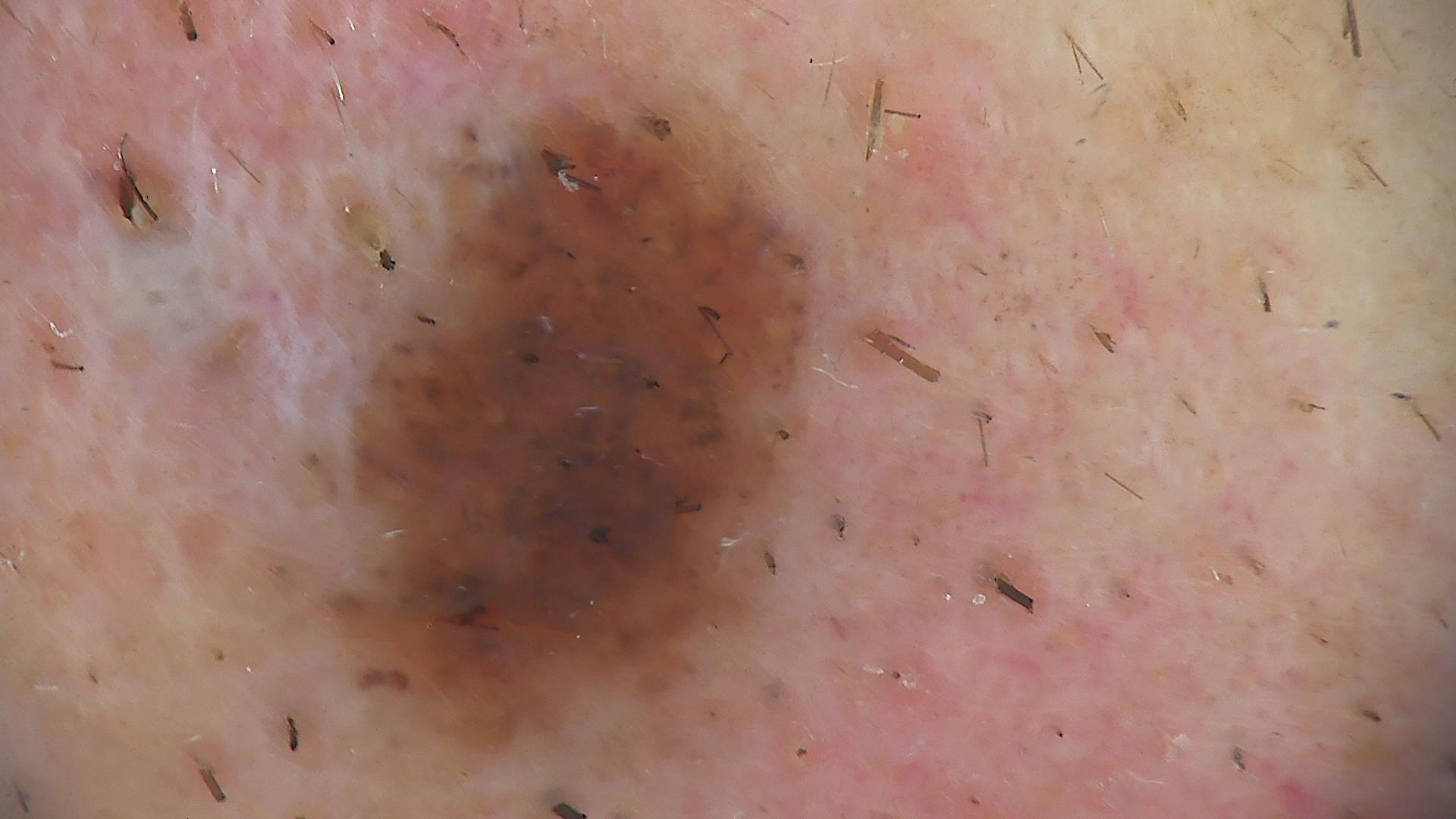Classified as a congenital compound nevus.